The patient is Fitzpatrick phototype II · a female patient about 35 years old · a skin lesion imaged with a dermatoscope: 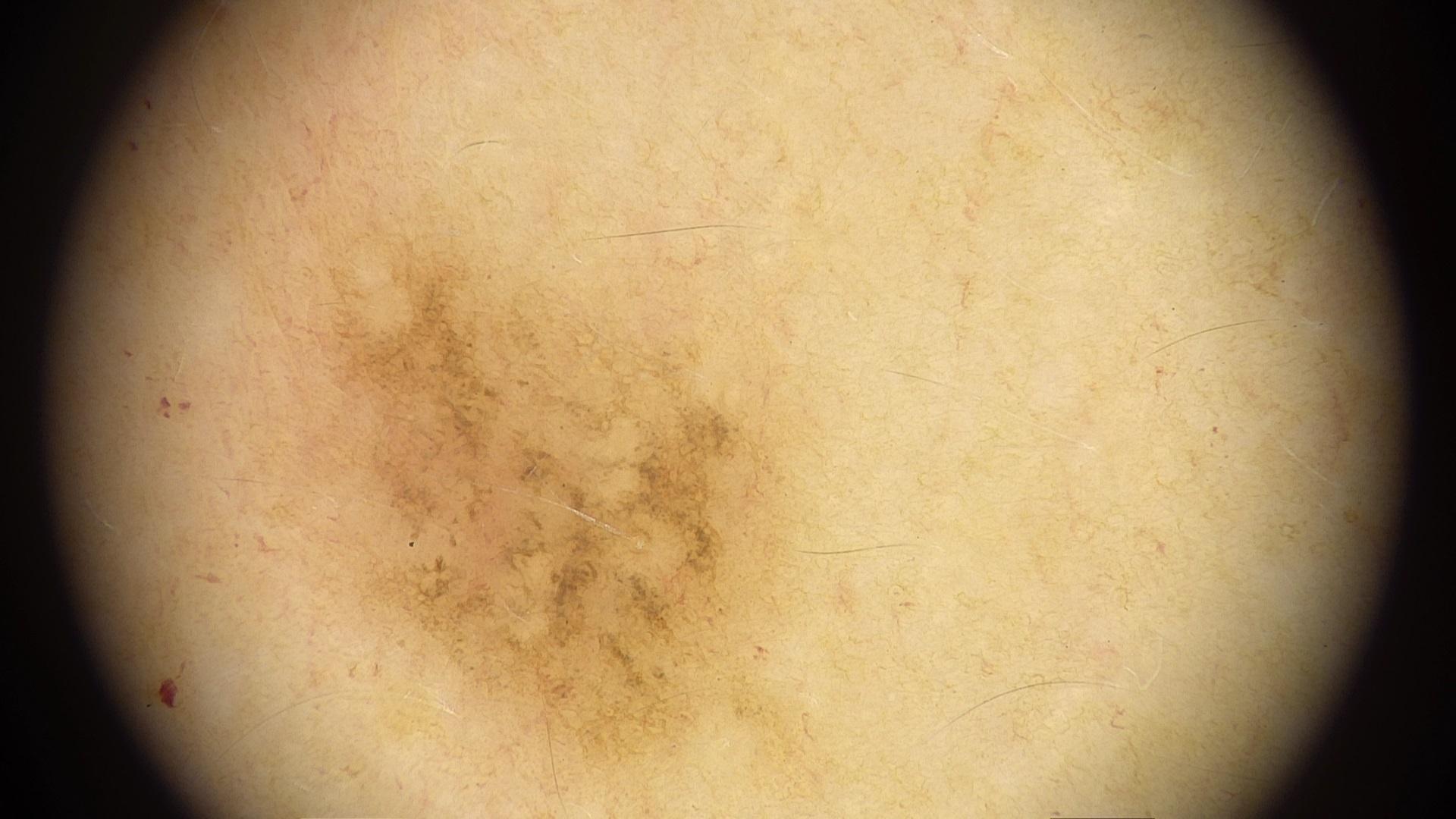The clinical impression was a benign lesion — a nevus.